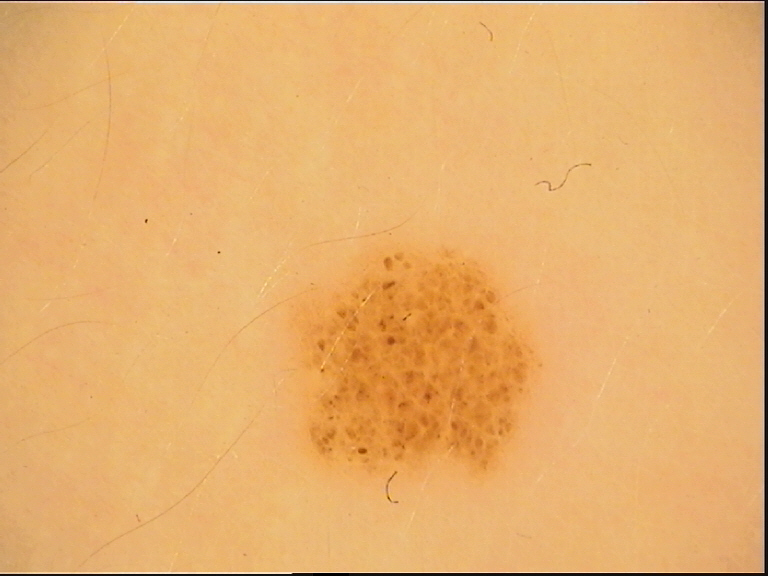Case: A dermoscopic image of a skin lesion. The architecture is that of a banal lesion. Conclusion: The diagnosis was a junctional nevus.